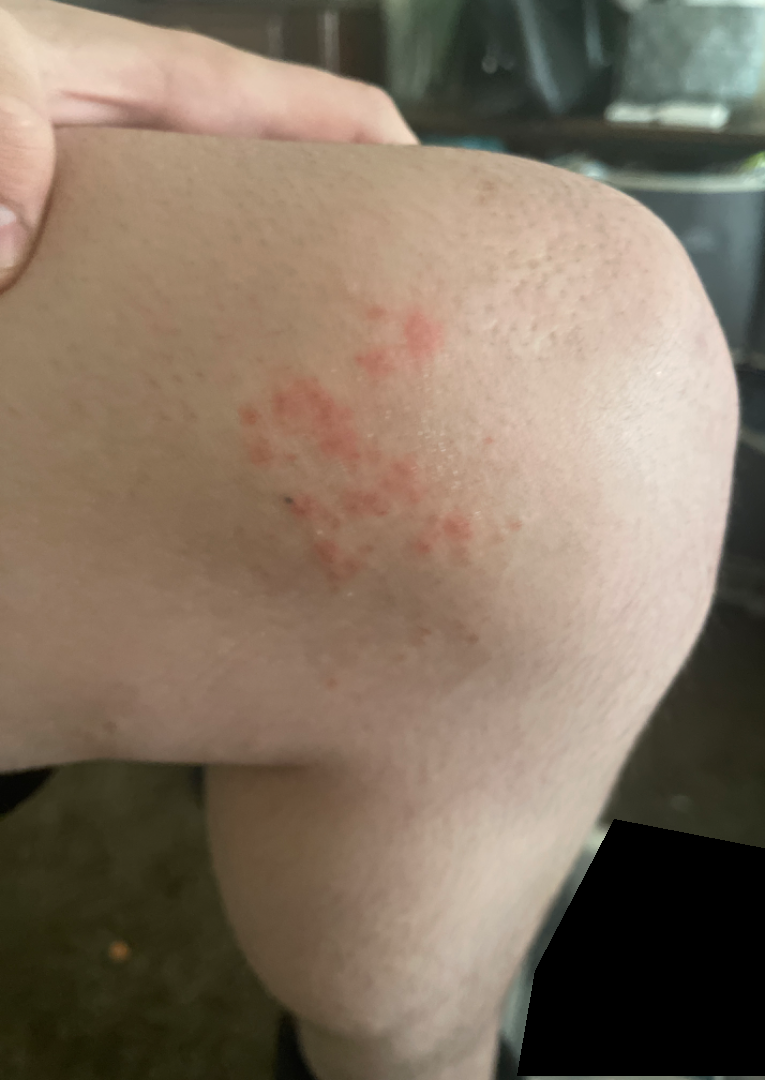Review: The case was difficult to assess from the available photograph. Patient information: The subject is 18–29, male. The photograph is a close-up of the affected area.